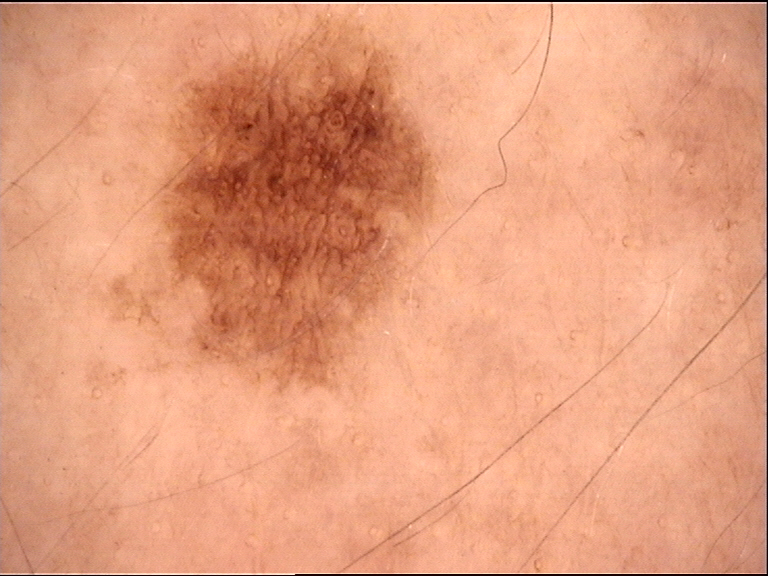A dermoscopic image of a skin lesion. Consistent with a dysplastic junctional nevus.